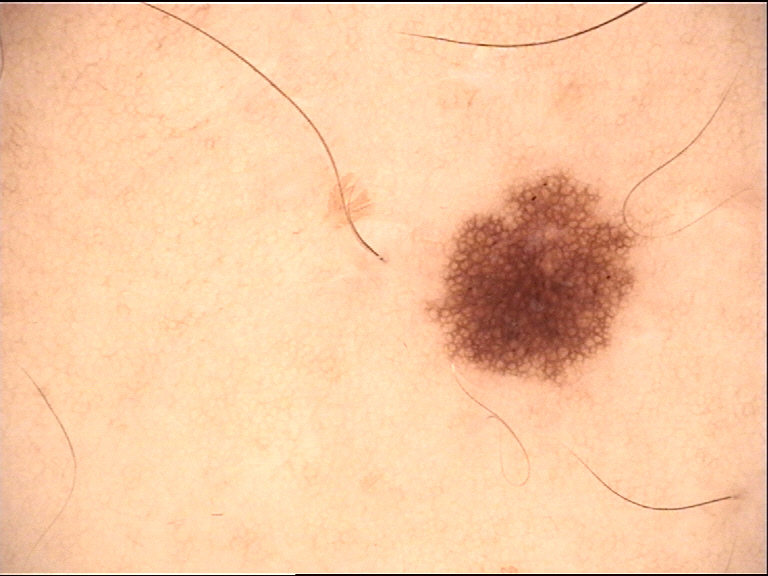image type = dermoscopy
subtype = banal
diagnosis = junctional nevus (expert consensus)